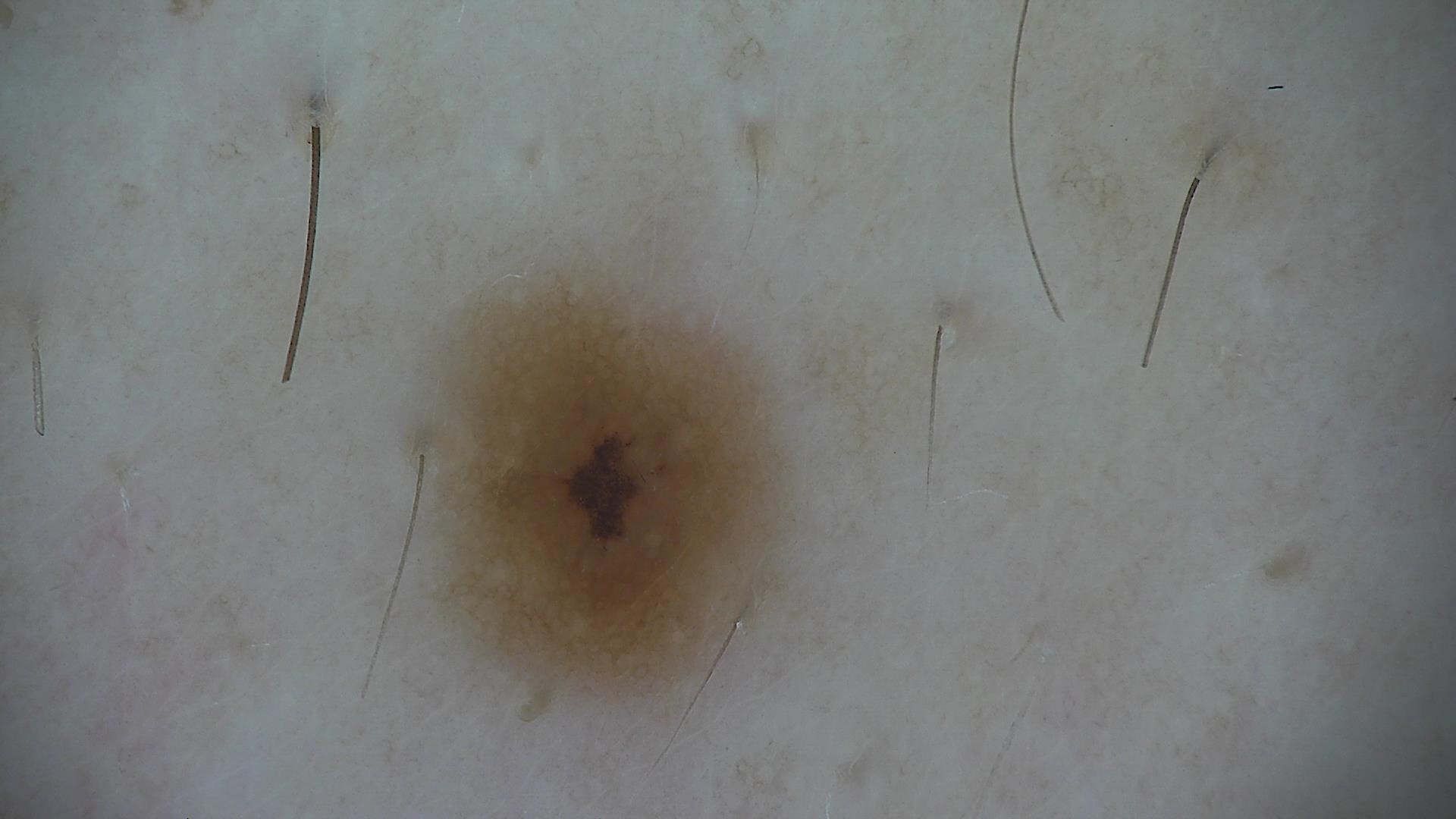The diagnosis was a dysplastic junctional nevus.